A dermoscopy image of a single skin lesion: 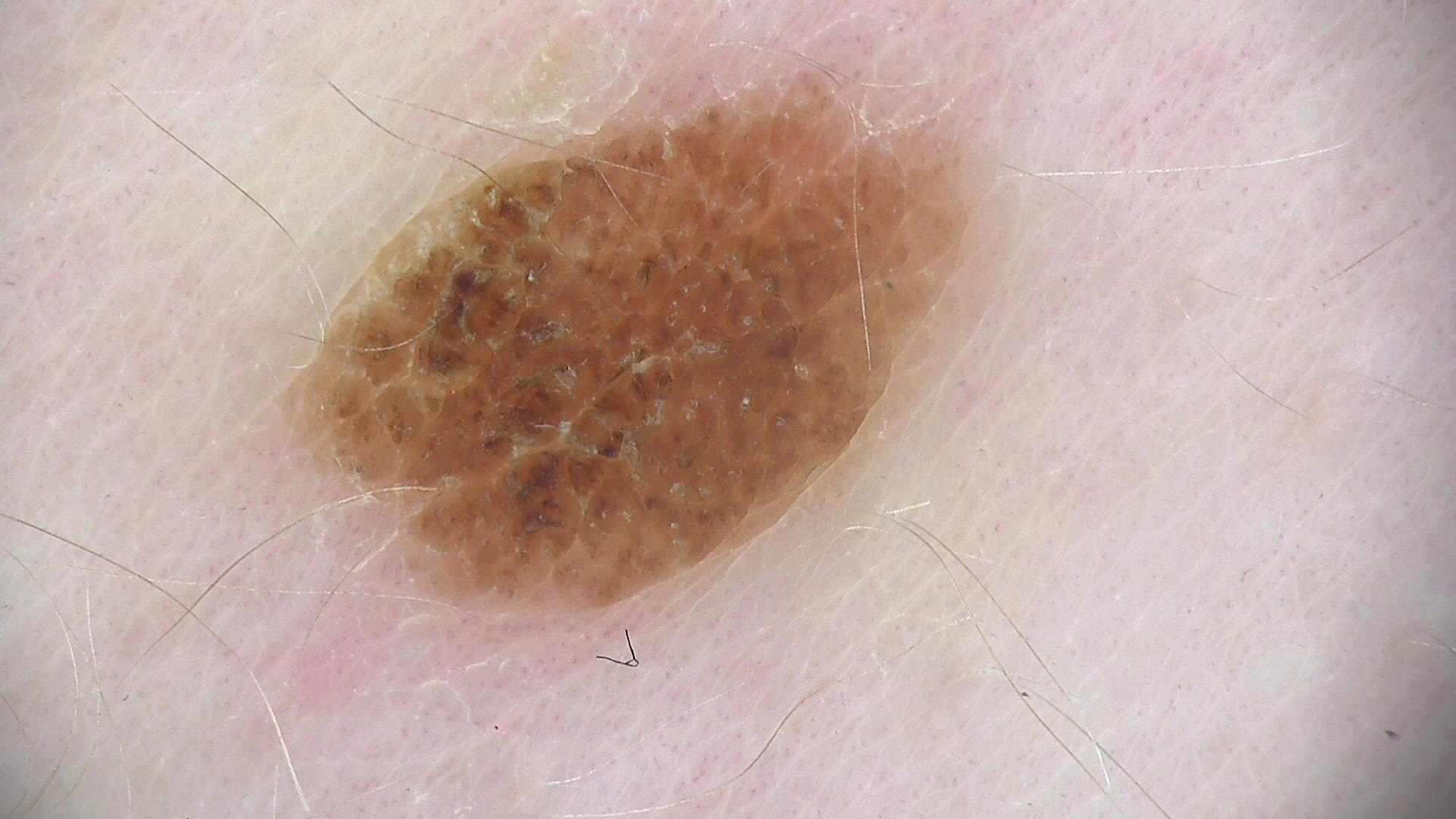assessment: compound nevus (expert consensus)